A dermoscopy image of a single skin lesion:
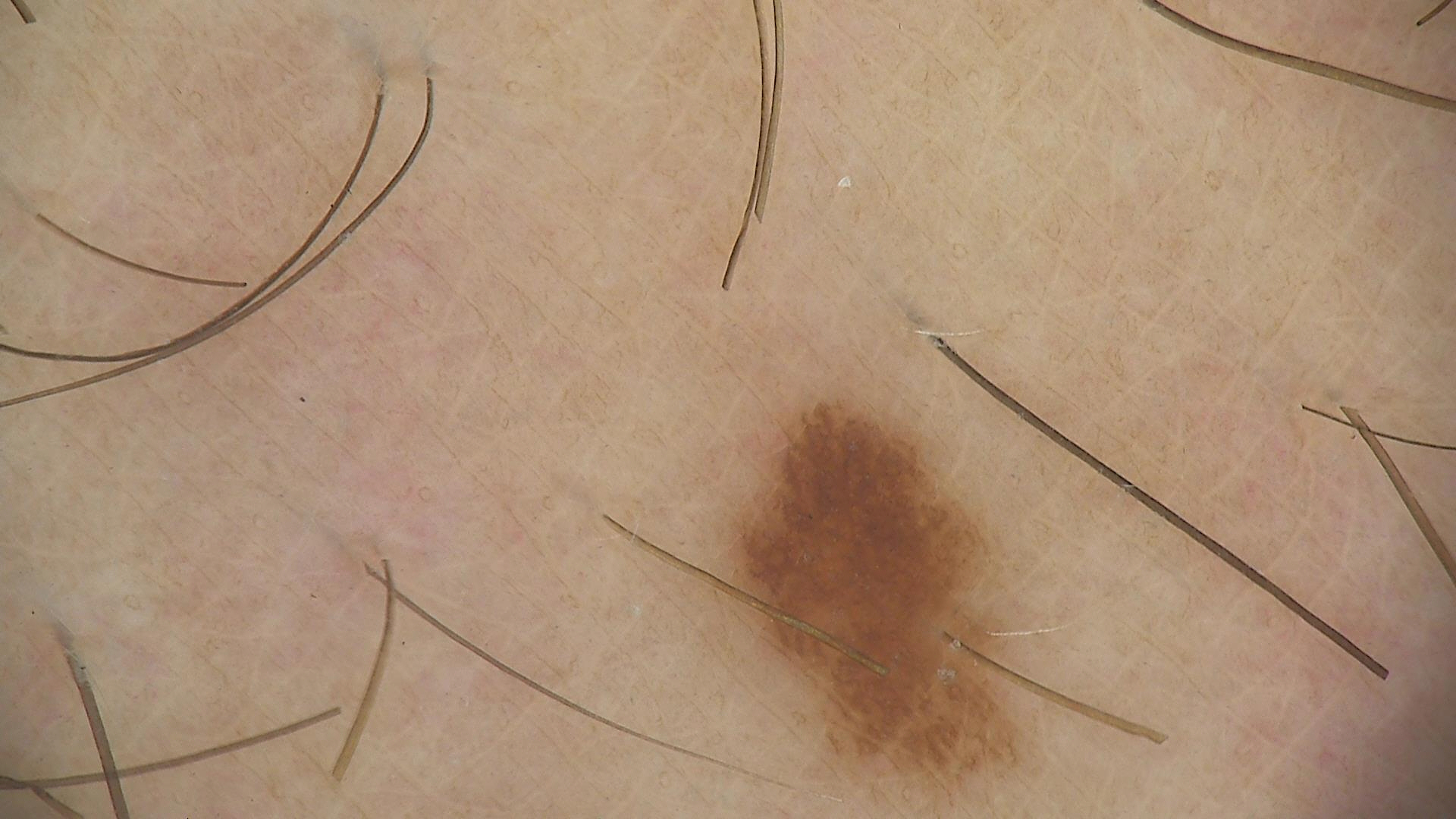The diagnostic label was a banal lesion — a junctional nevus.